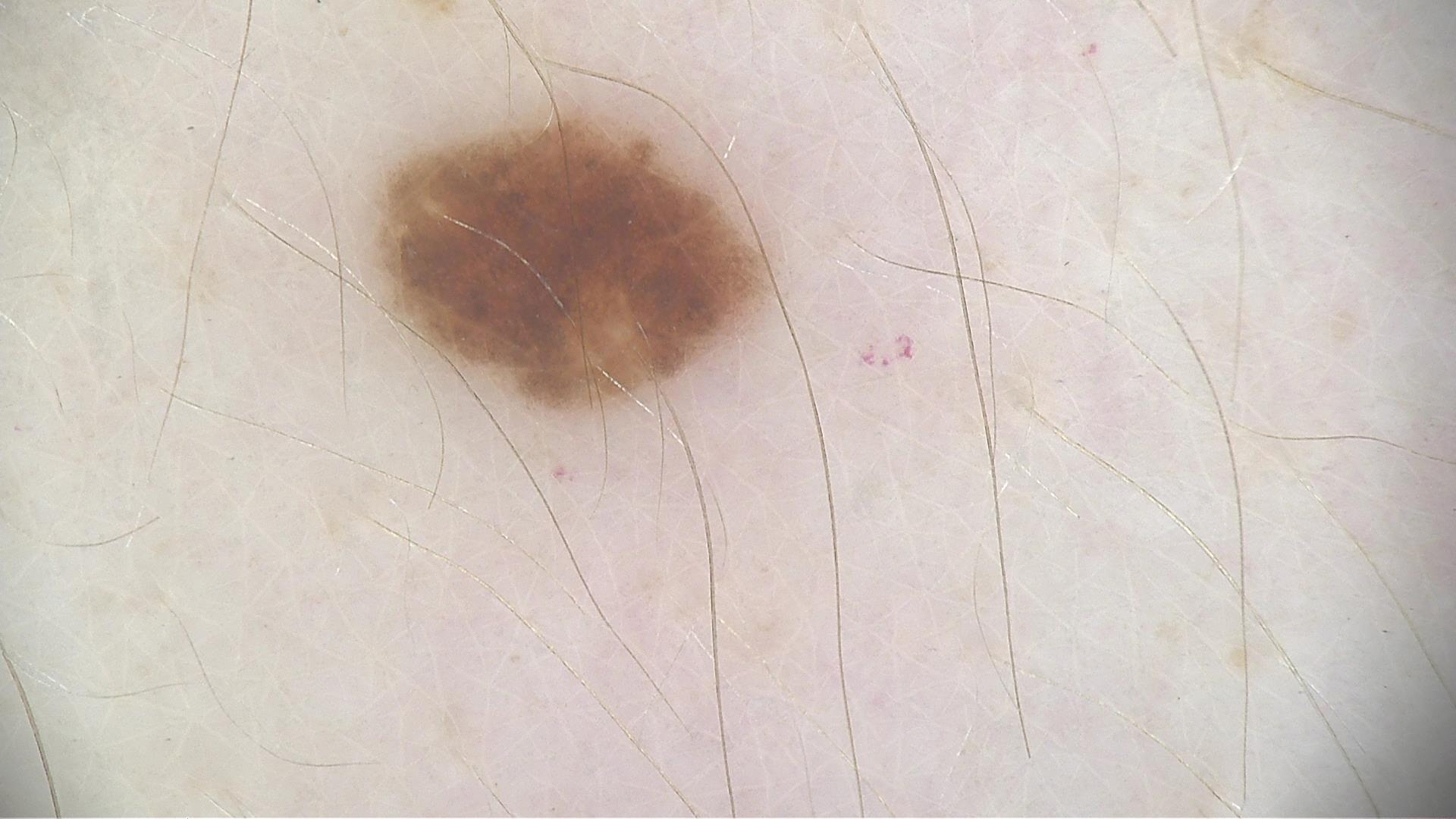Q: What is the imaging modality?
A: dermatoscopy
Q: What was the diagnostic impression?
A: dysplastic junctional nevus (expert consensus)